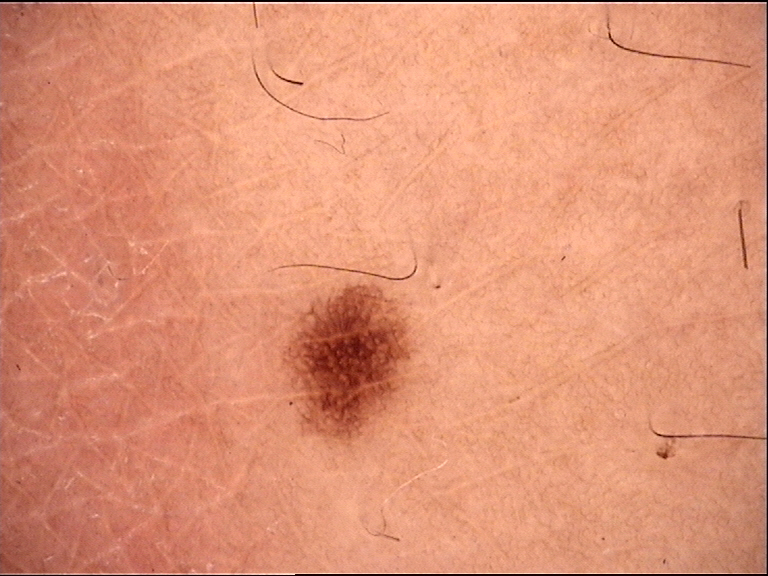A dermatoscopic image of a skin lesion.
Diagnosed as a banal lesion — a junctional nevus.